A female patient in their 30s; the patient is FST III; per the chart, no melanoma in first-degree relatives and no previous melanoma; a dermatoscopic image of a skin lesion: 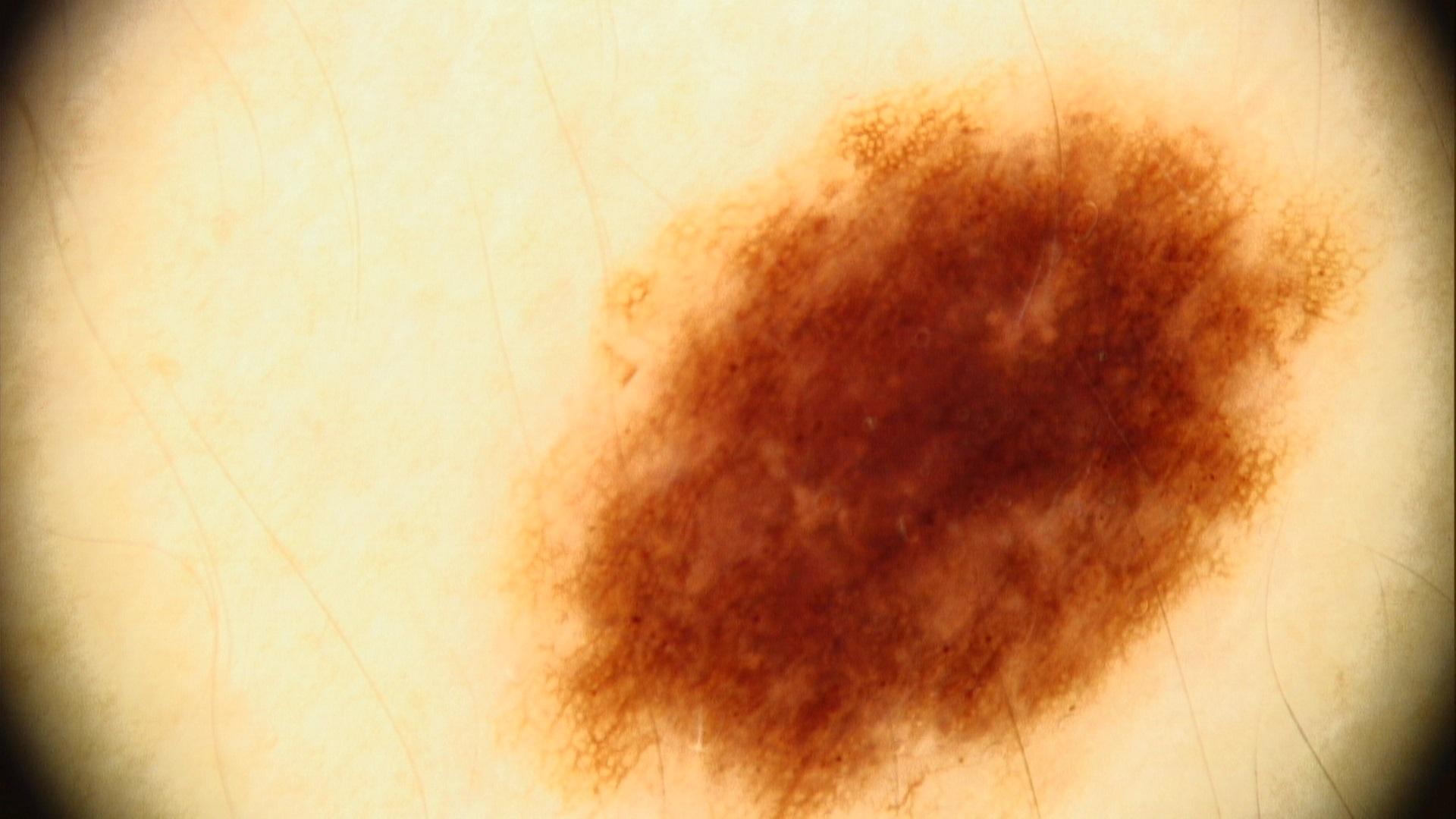Summary: The lesion is on the trunk. Impression: The clinical assessment was a benign, melanocytic lesion — a nevus.